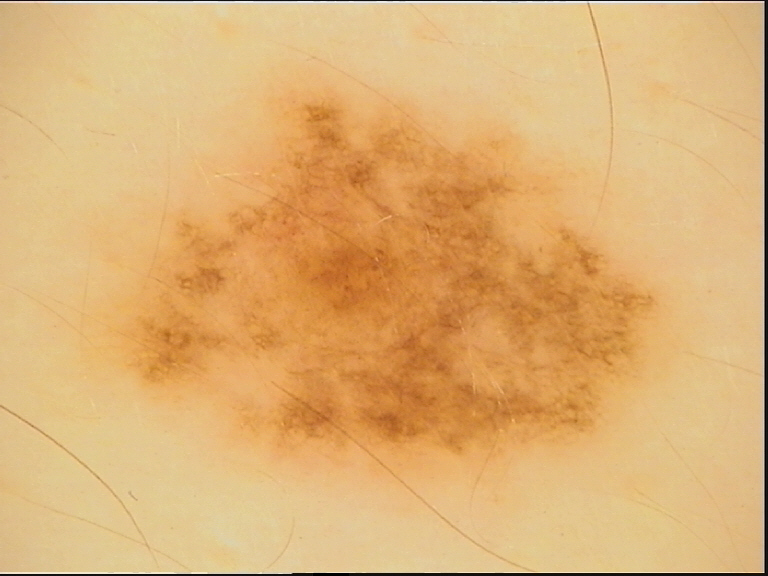A dermoscopic close-up of a skin lesion. The diagnostic label was a dysplastic junctional nevus.